The head or neck is involved. The patient indicates enlargement. The patient indicates the lesion is raised or bumpy. This image was taken at a distance. The patient indicates the condition has been present for about one day. Female contributor, age 40–49. No associated systemic symptoms reported — 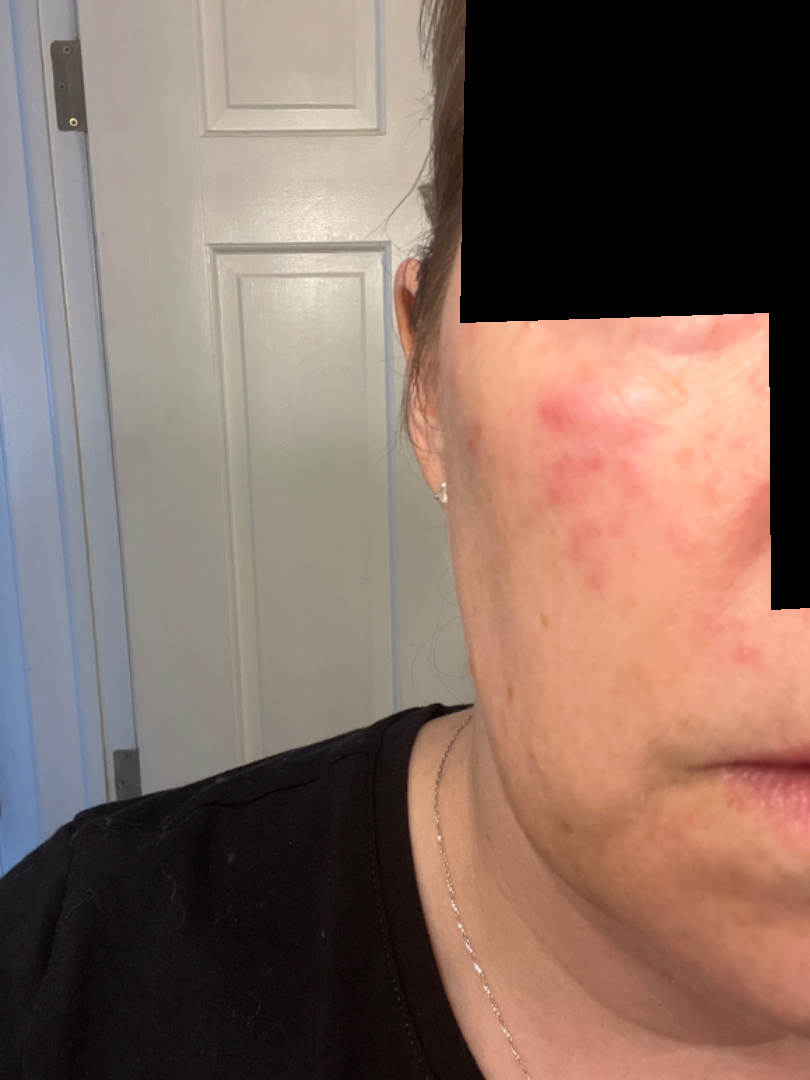differential diagnosis = Acne (0.60); Rosacea (0.40).